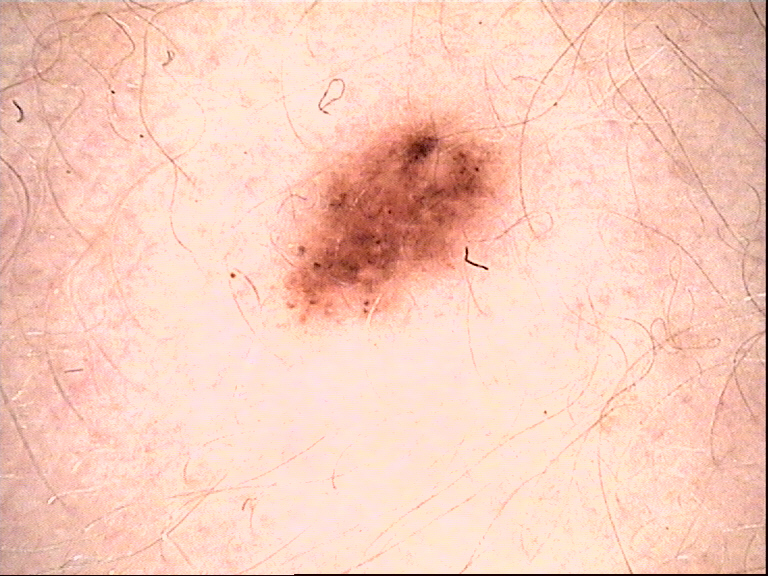Findings:
A skin lesion imaged with a dermatoscope.
Impression:
Classified as a benign lesion — a dysplastic junctional nevus.